The affected area is the top or side of the foot, palm, leg and sole of the foot. The contributor is a female aged 18–29. This is a close-up image.
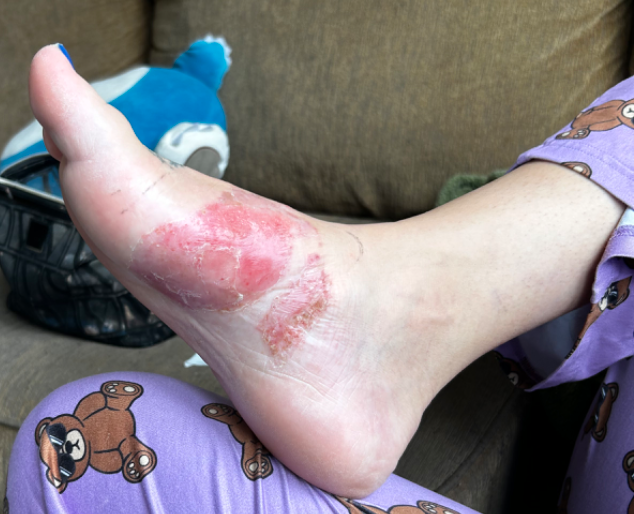assessment = indeterminate.